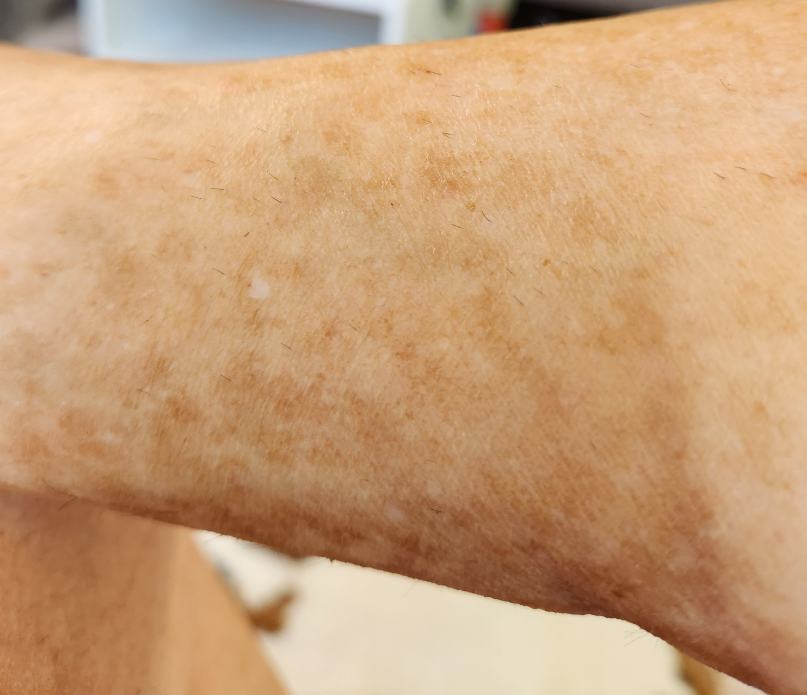This is a close-up image.
The patient is a male aged 50–59.
Most consistent with Pigmented purpuric eruption.